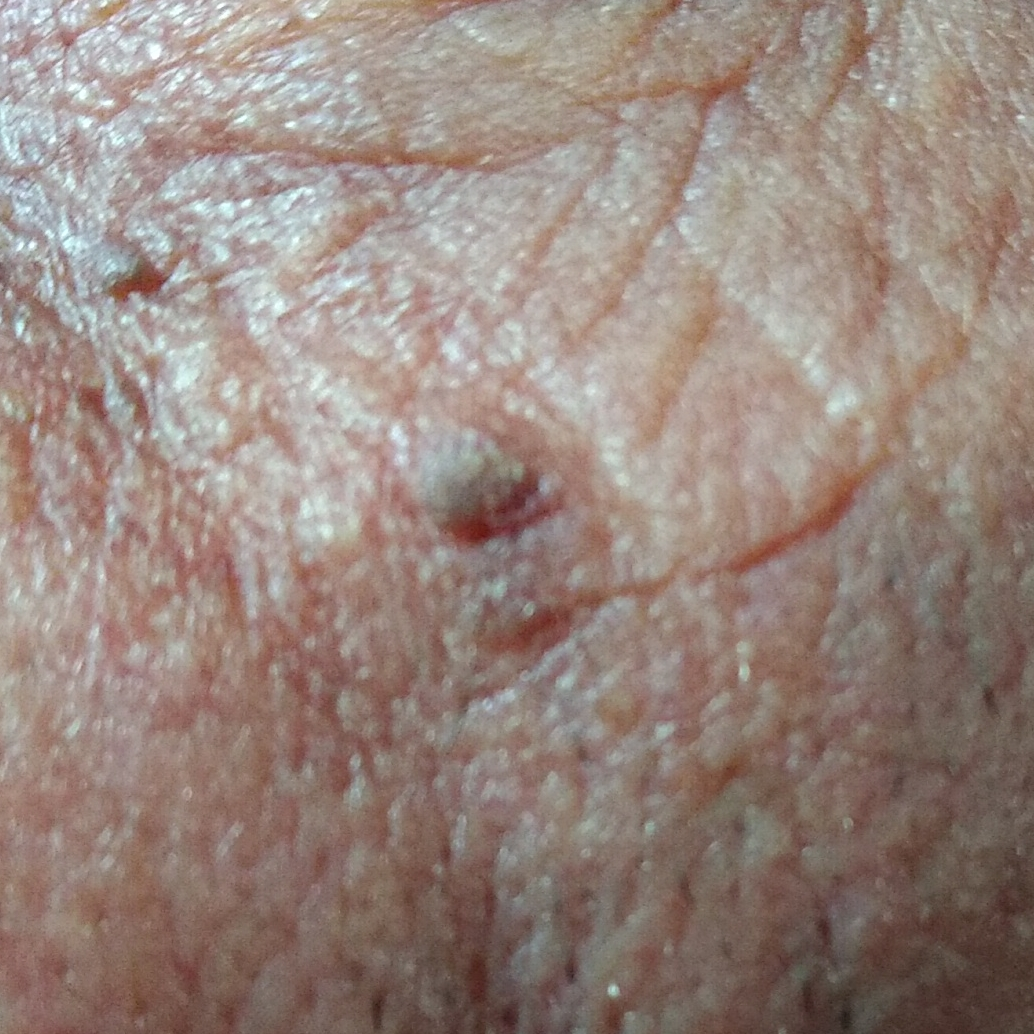A smartphone photograph of a skin lesion. By the patient's account, the lesion is elevated, but has not changed and does not itch. Consistent with a seborrheic keratosis.